A female patient, approximately 80 years of age. A dermoscopic close-up of a skin lesion: 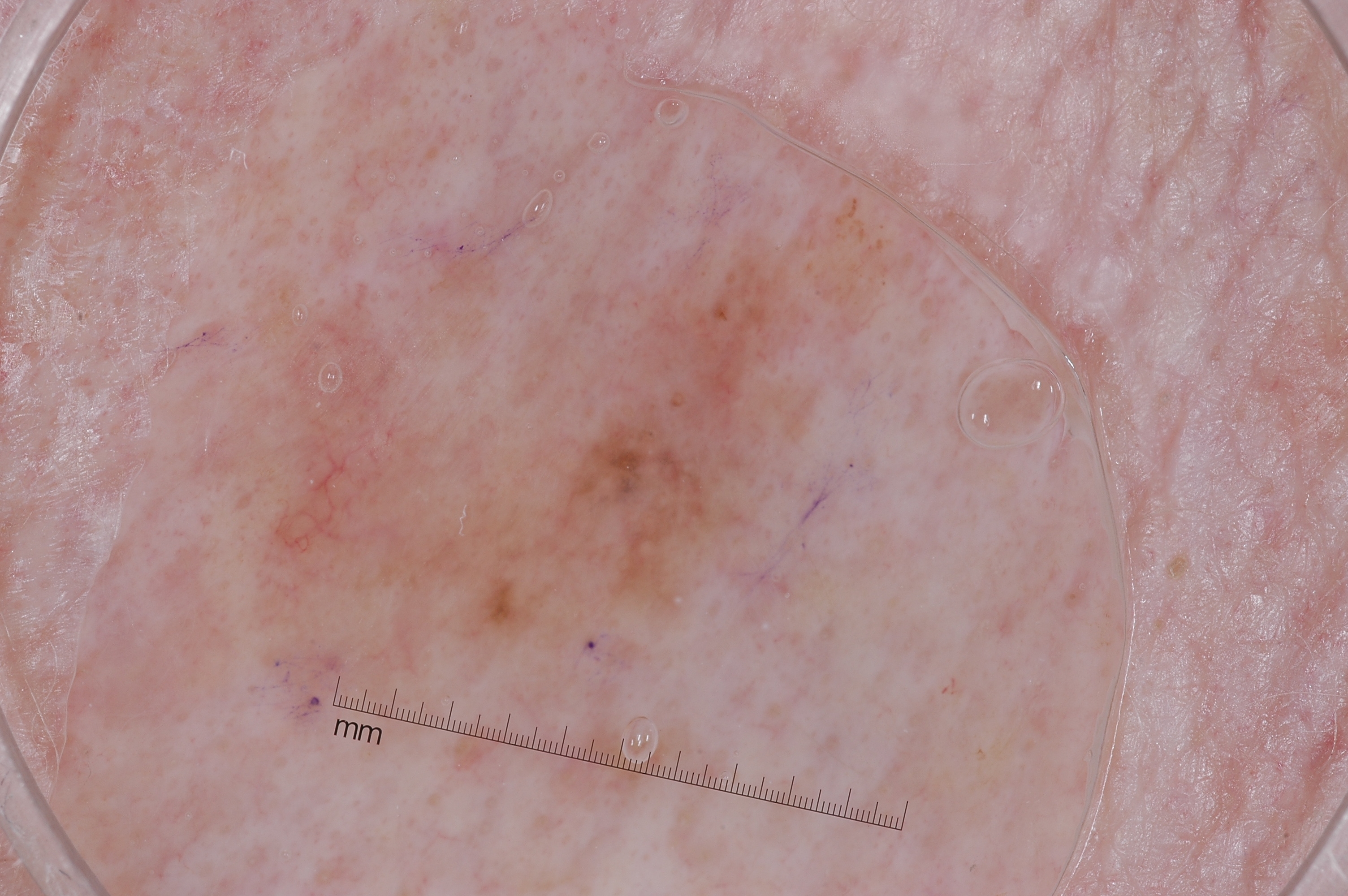{
  "lesion_extent": "moderate",
  "dermoscopic_features": {
    "present": [
      "milia-like cysts"
    ],
    "absent": [
      "pigment network",
      "negative network",
      "streaks"
    ]
  },
  "lesion_location": {
    "bbox_xyxy": [
      186,
      182,
      894,
      773
    ]
  },
  "diagnosis": {
    "name": "melanoma",
    "malignancy": "malignant",
    "lineage": "melanocytic",
    "provenance": "histopathology"
  }
}